The photo was captured at a distance.
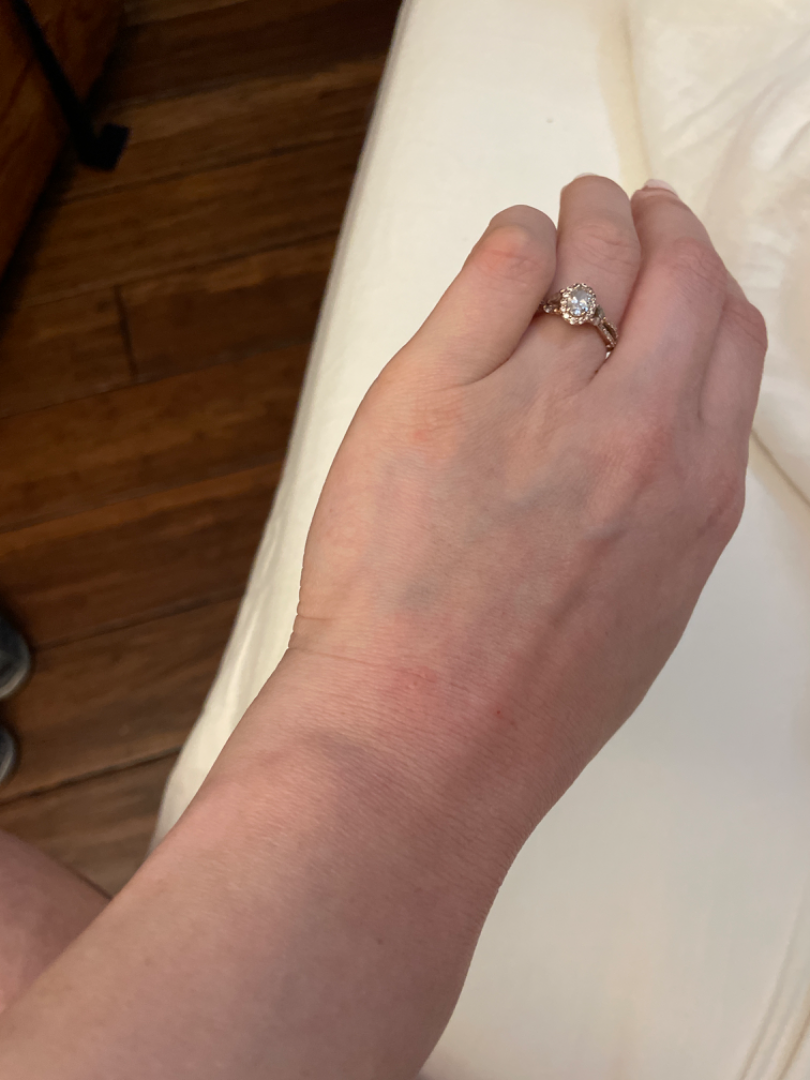<case>
  <differential>
    <leading>Insect Bite</leading>
  </differential>
</case>